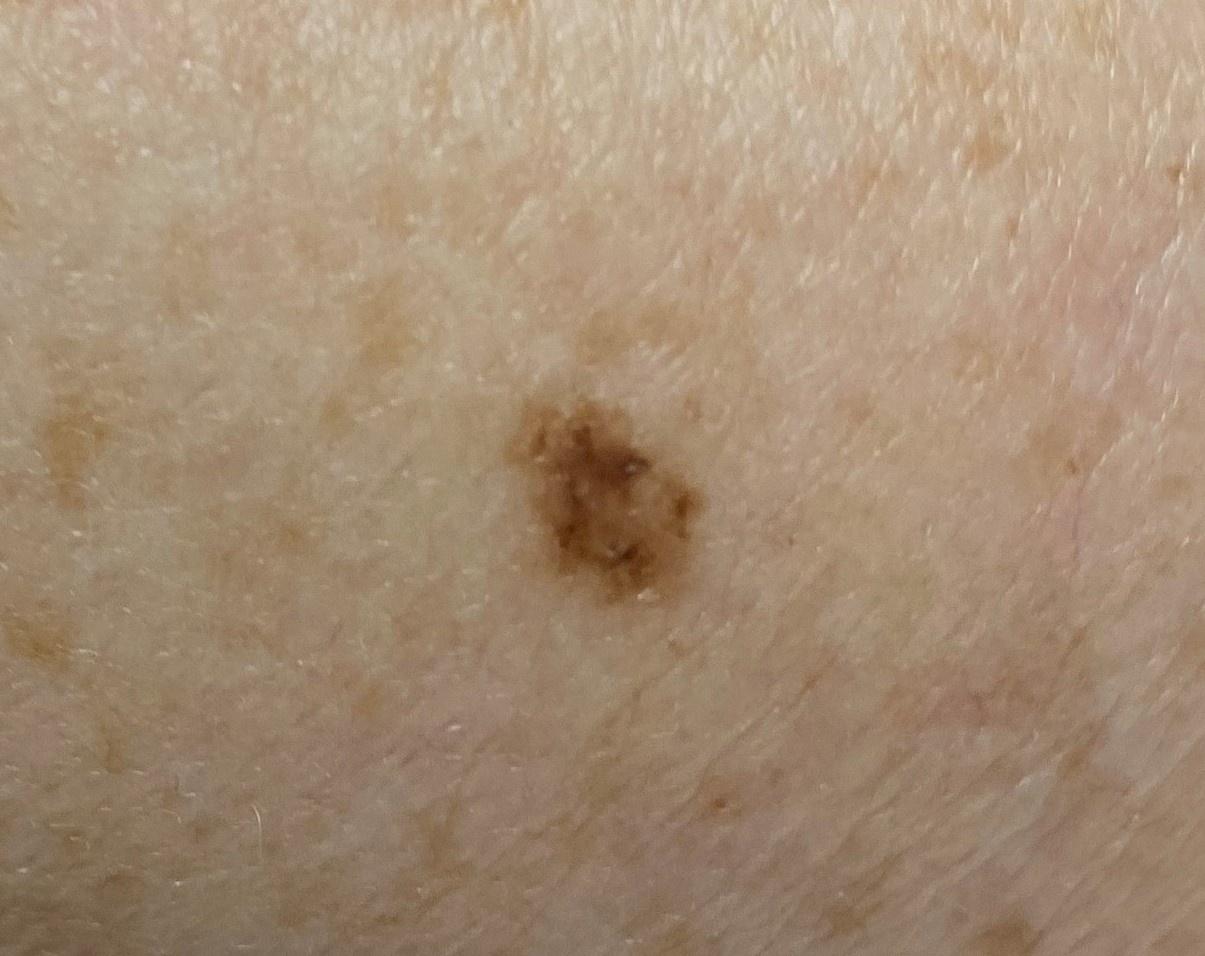Q: What does the history note?
A: a previous melanoma
Q: What Fitzpatrick skin type was recorded?
A: II
Q: What are the patient's age and sex?
A: female, in their mid- to late 70s
Q: What kind of image is this?
A: clinical overview photograph
Q: Where is the lesion located?
A: an upper extremity
Q: What is the diagnosis?
A: Nevus (biopsy-proven)